Texture is reported as fluid-filled and raised or bumpy · located on the head or neck · close-up view · the patient considered this acne · female patient, age 50–59:
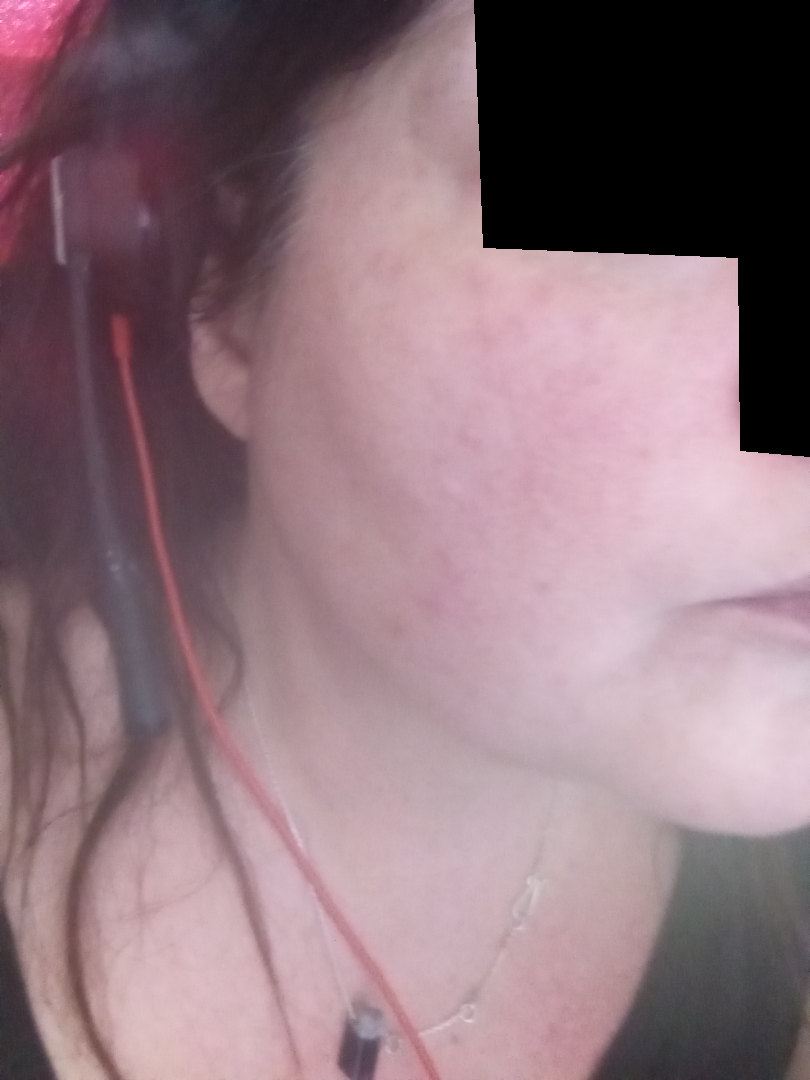dermatologist impression=Rosacea (67%); Acne (33%).